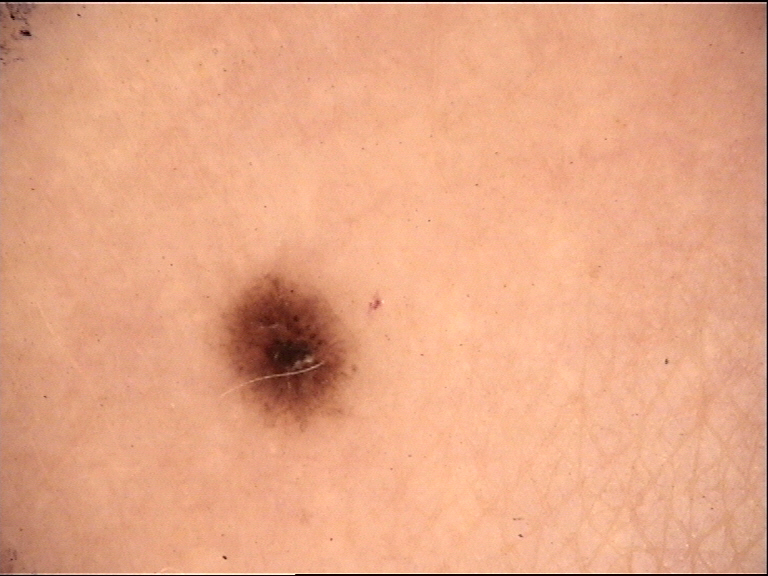Q: What kind of image is this?
A: dermatoscopy
Q: What is this lesion?
A: dysplastic junctional nevus (expert consensus)